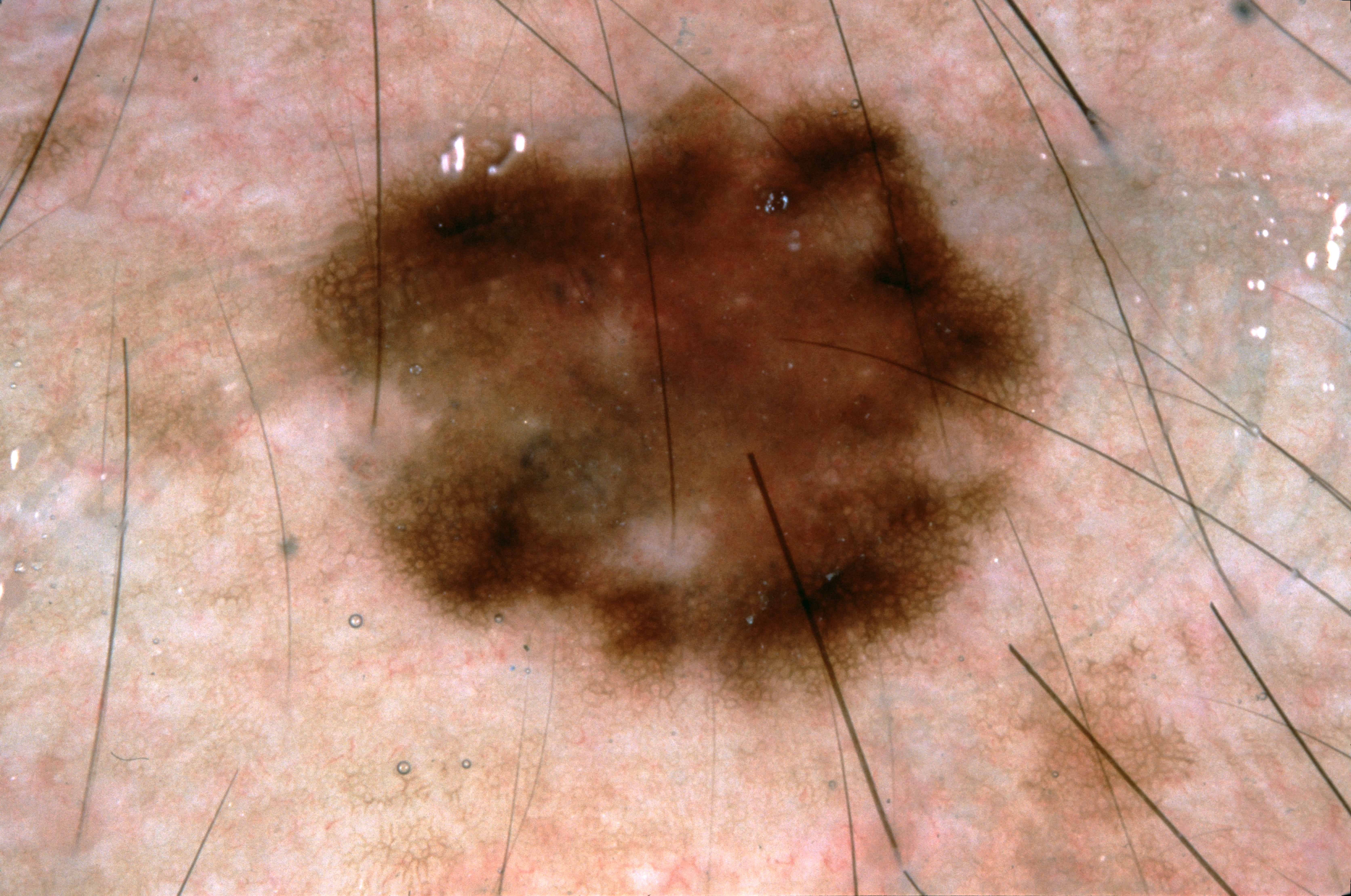Image and clinical context: A dermoscopic view of a skin lesion. The lesion takes up about 35% of the image. Dermoscopy demonstrates pigment network. With coordinates (x1, y1, x2, y2), the lesion's extent is [299,54,1076,742]. Assessment: Consistent with a melanocytic nevus.